An image taken at an angle · the lesion involves the leg.
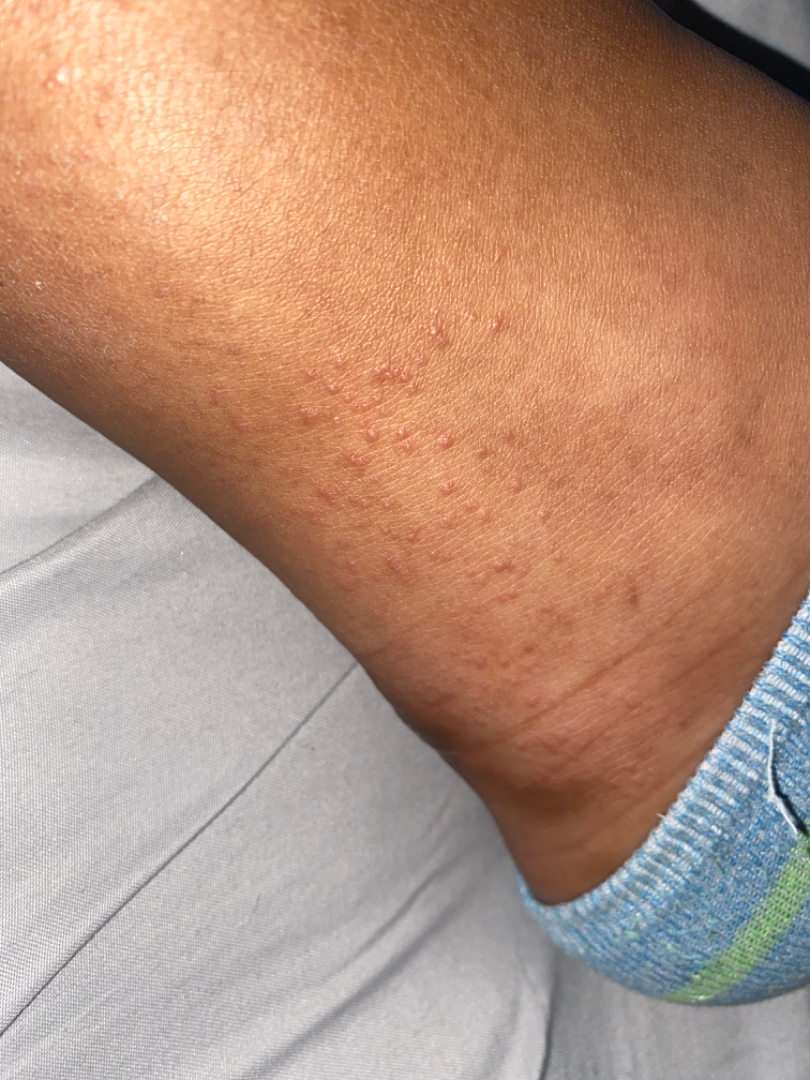Eczema (most likely); Lichen planus/lichenoid eruption (considered).